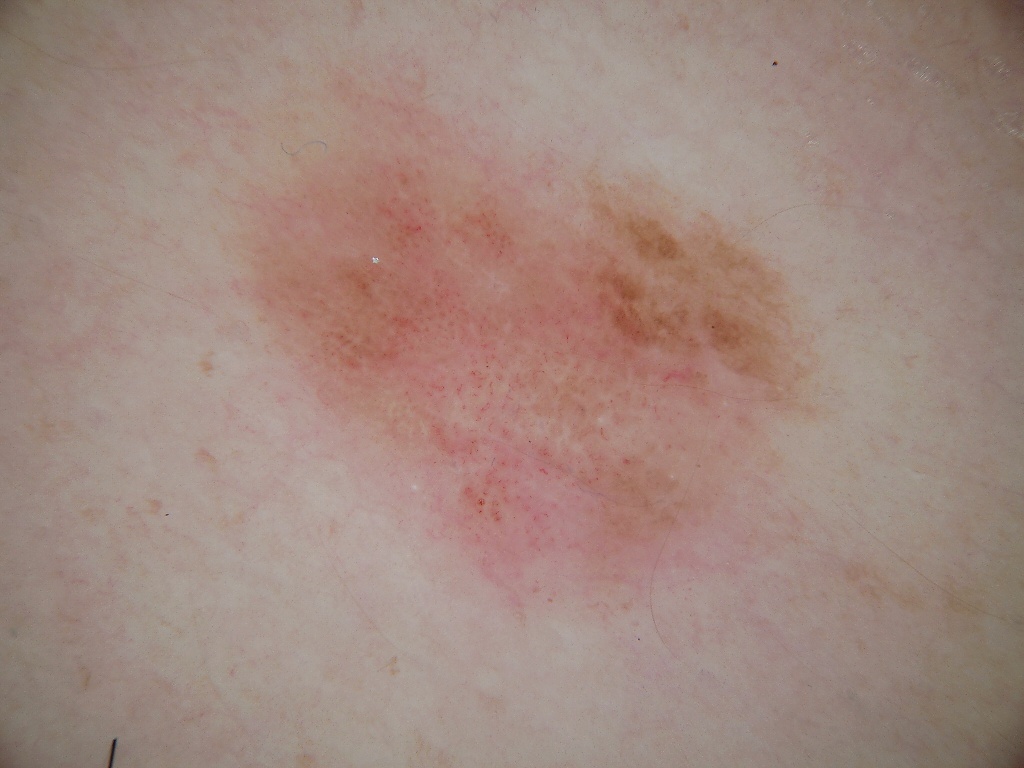imaging = dermoscopy | patient = female, aged 33 to 37 | extent = ~33% of the field | dermoscopic pattern = negative network, globules, and milia-like cysts | lesion location = 182, 42, 847, 637 | impression = a melanocytic nevus.